A skin lesion imaged with a dermatoscope; a female patient aged 84; acquired for a research image collection, with no referral diagnosis: 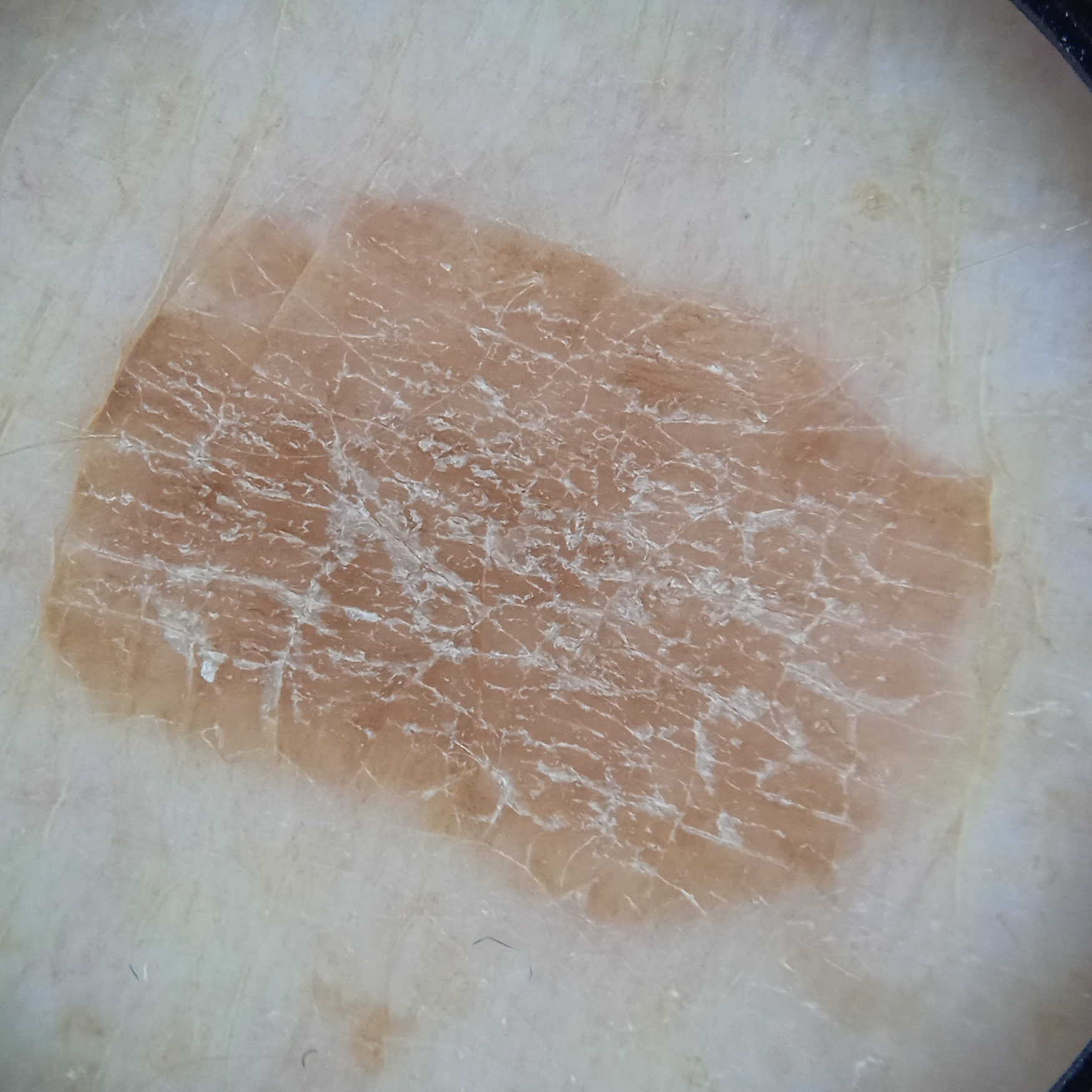anatomic site: an arm | lesion size: 11.2 mm | diagnostic label: seborrheic keratosis (dermatologist consensus).